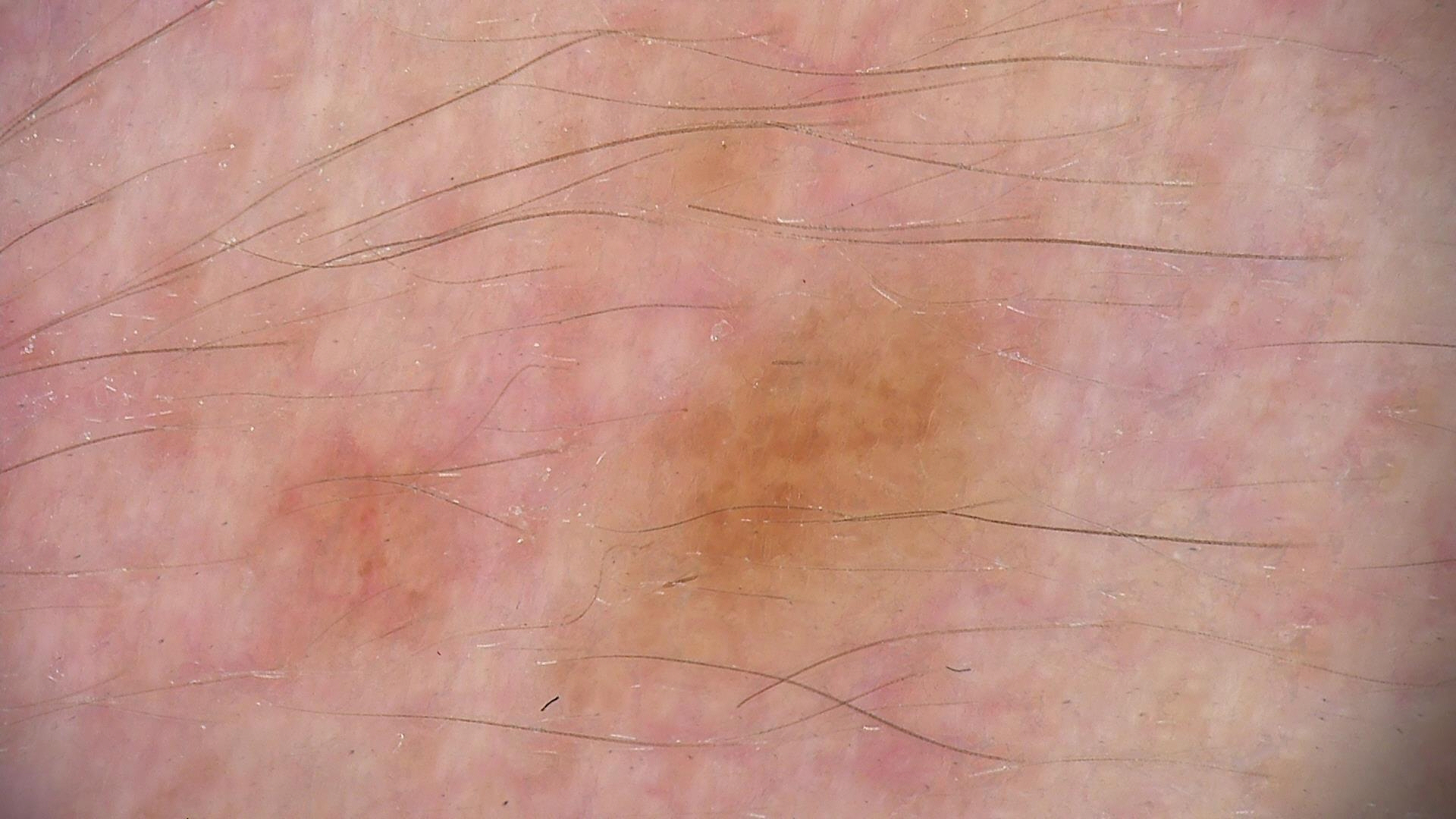Labeled as a dysplastic junctional nevus.